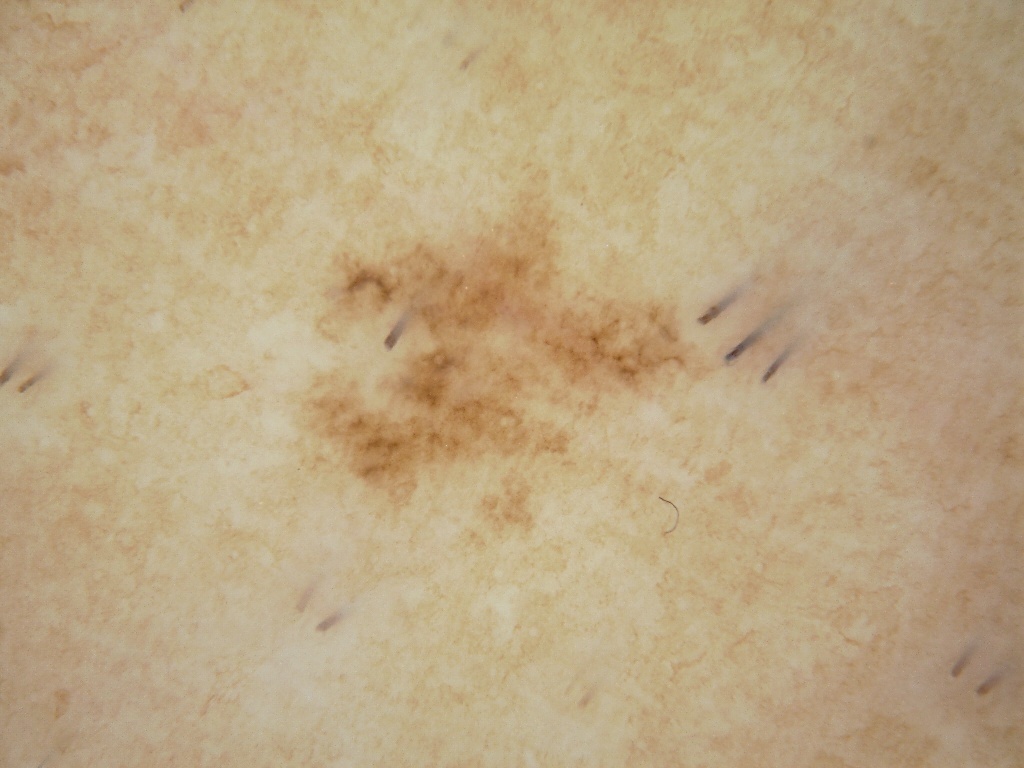image type=dermoscopy | patient=female, aged 43-47 | features=pigment network and milia-like cysts; absent: negative network, streaks, and globules | extent=~15% of the field | lesion bbox=box(287, 179, 719, 553) | impression=a melanocytic nevus.